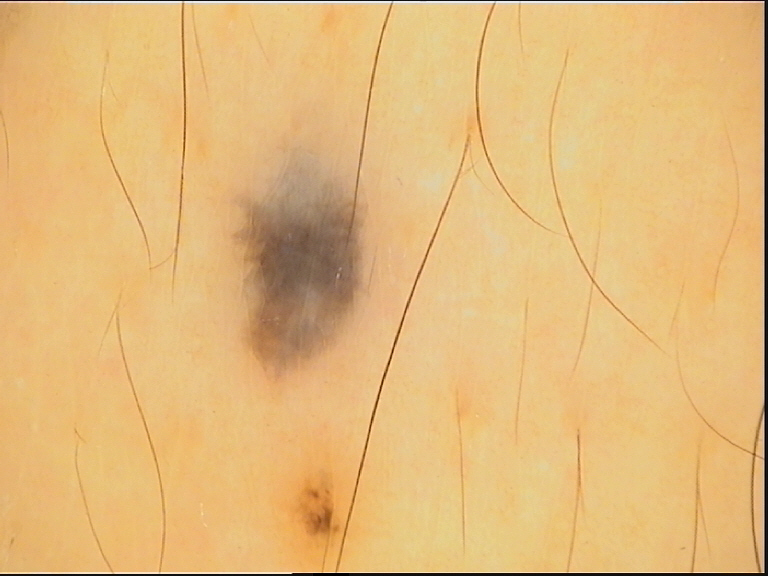A dermoscopy image of a single skin lesion. Labeled as a dermal lesion — a blue nevus.